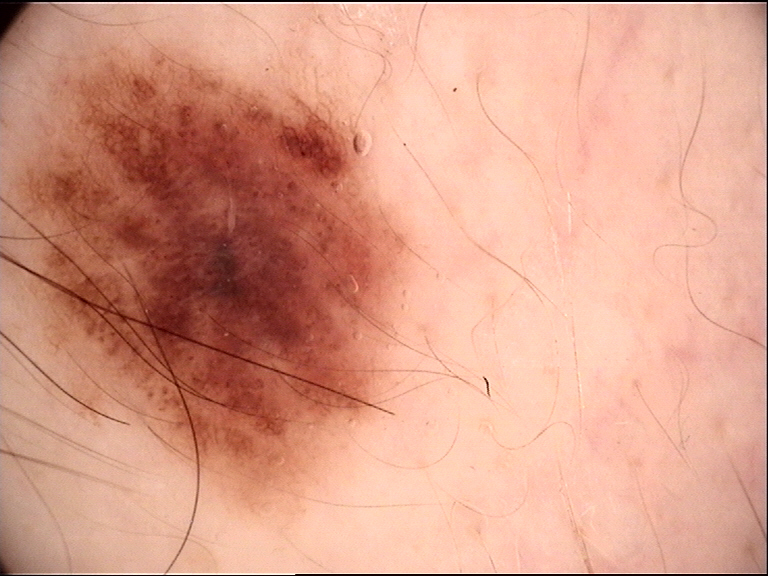A dermoscopy image of a single skin lesion.
Consistent with a benign lesion — a dysplastic compound nevus.